Reported duration is one to three months; the patient reports the lesion is flat; located on the leg; a close-up photograph — 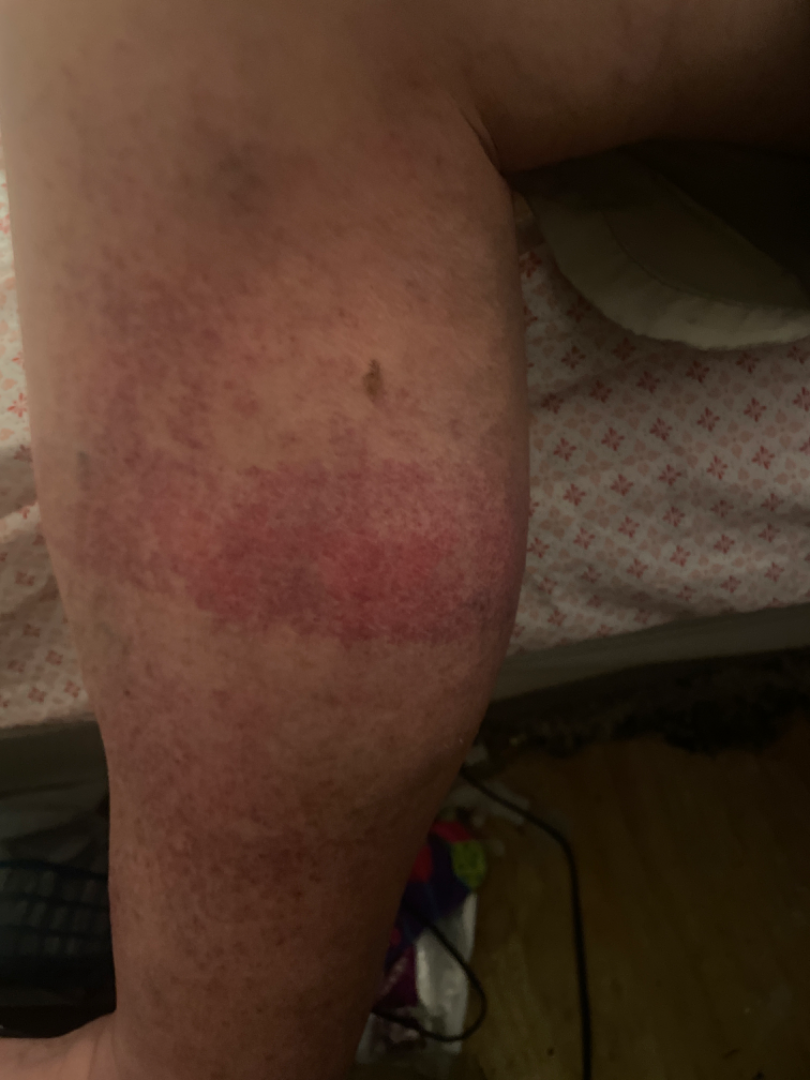– differential — in keeping with Vasculitis of the skin